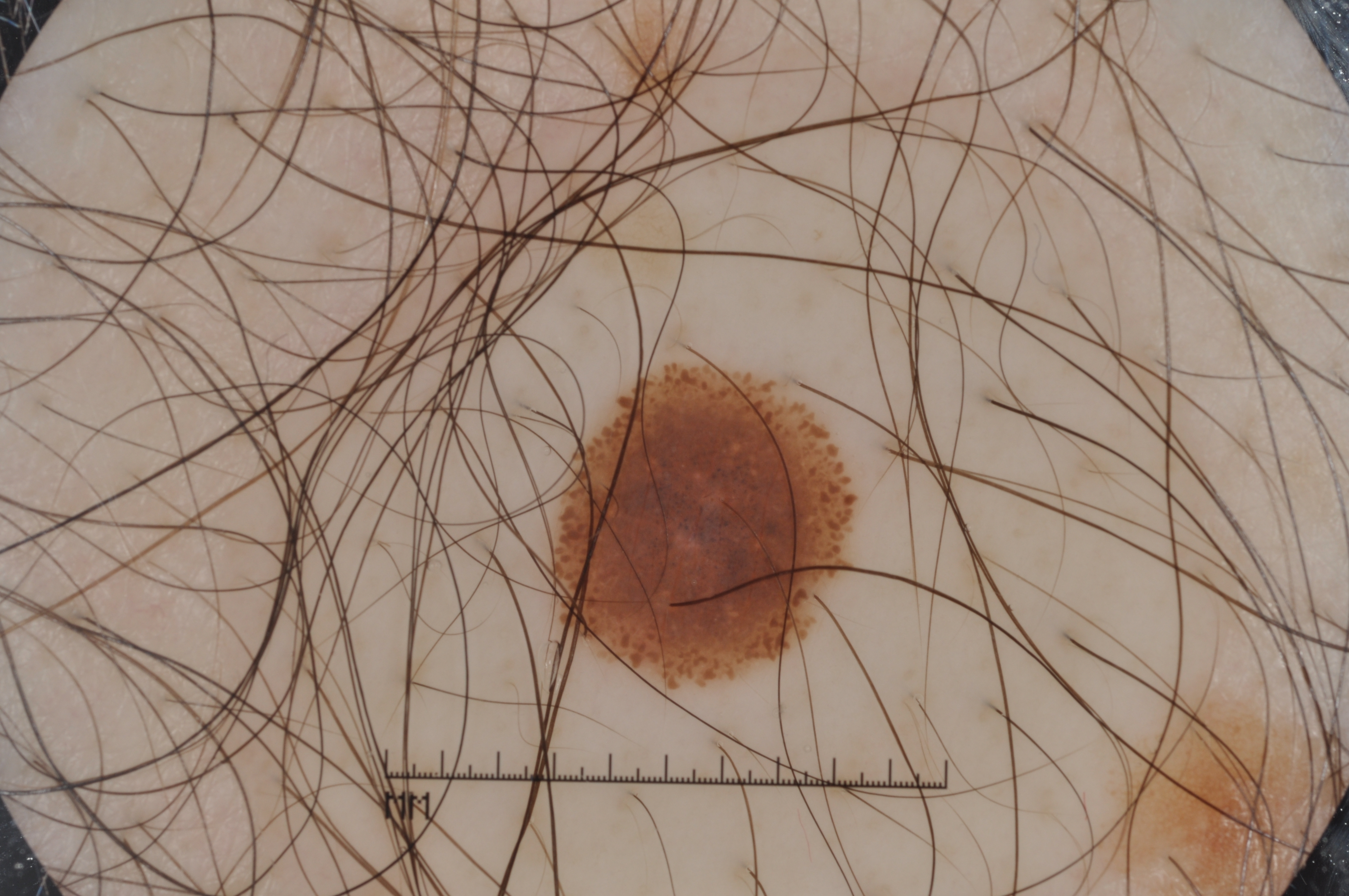A dermoscopic view of a skin lesion.
A male patient aged around 35.
The dermoscopic pattern shows no milia-like cysts, negative network, streaks, or pigment network.
As (left, top, right, bottom), the lesion is located at bbox(559, 365, 843, 679).
Diagnosed as a melanocytic nevus.